The lesion is associated with itching and pain; self-reported Fitzpatrick phototype VI; the contributor notes the lesion is rough or flaky; the patient is a male aged 18–29; the photograph was taken at an angle; the back of the hand is involved; self-categorized by the patient as skin that appeared healthy to them.
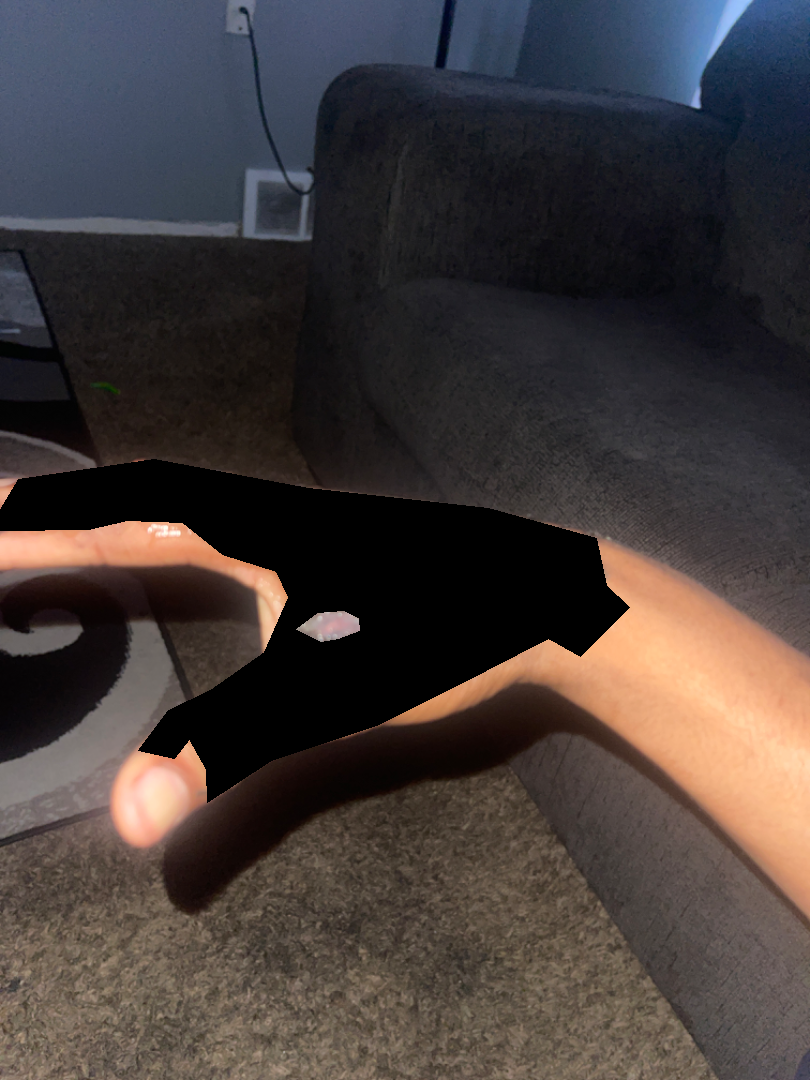assessment = indeterminate.